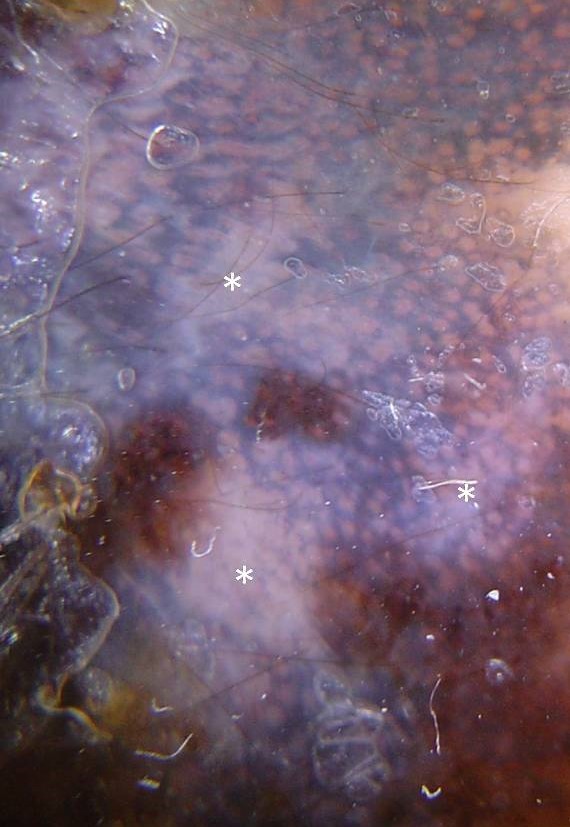A skin lesion imaged with a dermatoscope.
Histopathologically confirmed as a malignancy — a lentigo maligna.